A dermatoscopic image of a skin lesion: 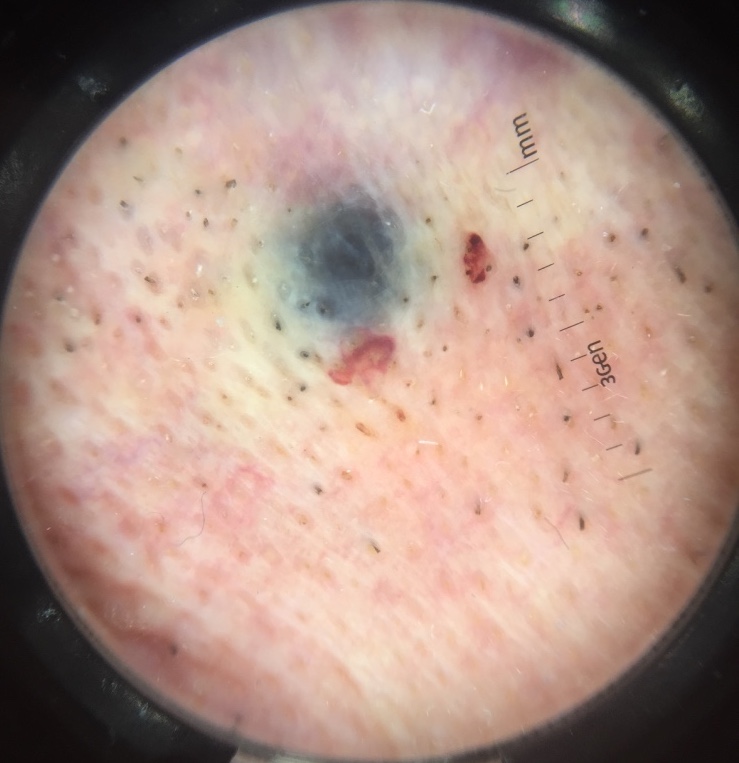diagnosis: blue nevus (expert consensus)